Close-up view. Located on the leg. The patient is 18–29, female:
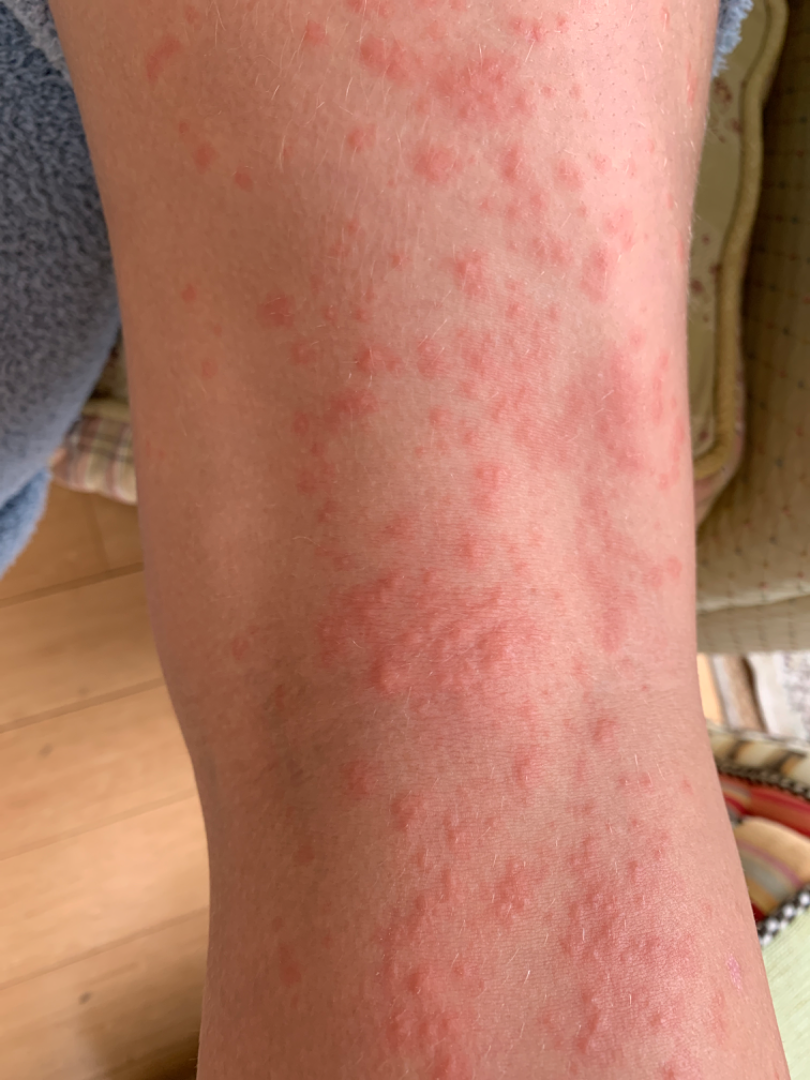Case summary:
• assessment — unable to determine